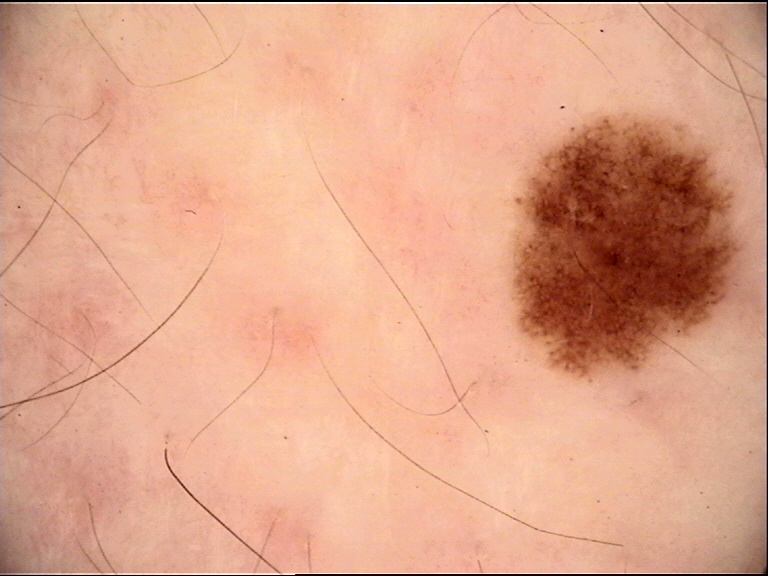Diagnosed as a dysplastic junctional nevus.